A dermoscopic view of a skin lesion.
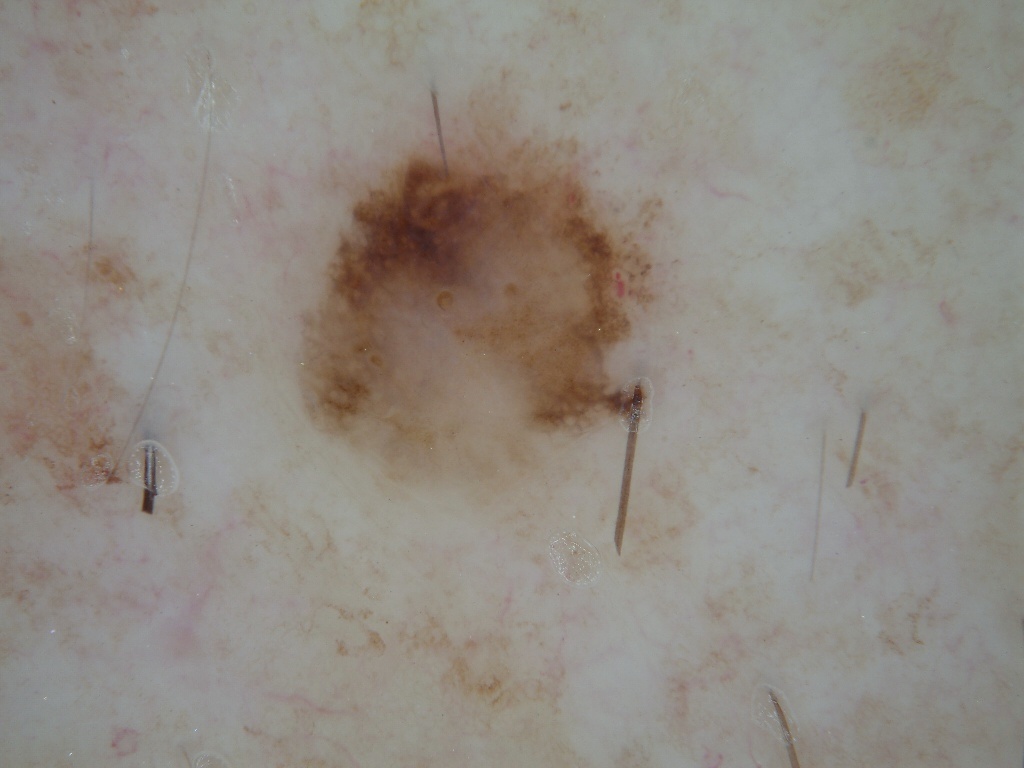lesion extent = ~18% of the field
lesion location = [278,71,686,551]
dermoscopic features = pigment network; absent: milia-like cysts, streaks, globules, and negative network
impression = a melanoma, a malignancy